The photograph is a close-up of the affected area.
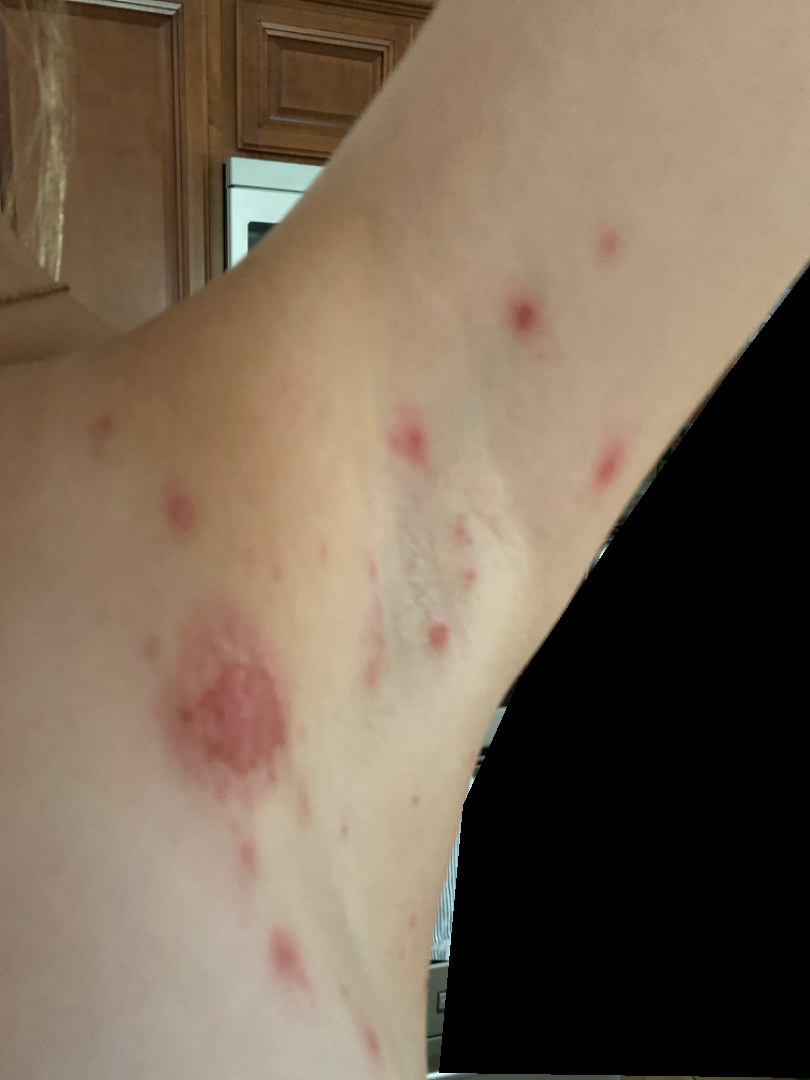| key | value |
|---|---|
| impression | most consistent with Impetigo; an alternative is Folliculitis |